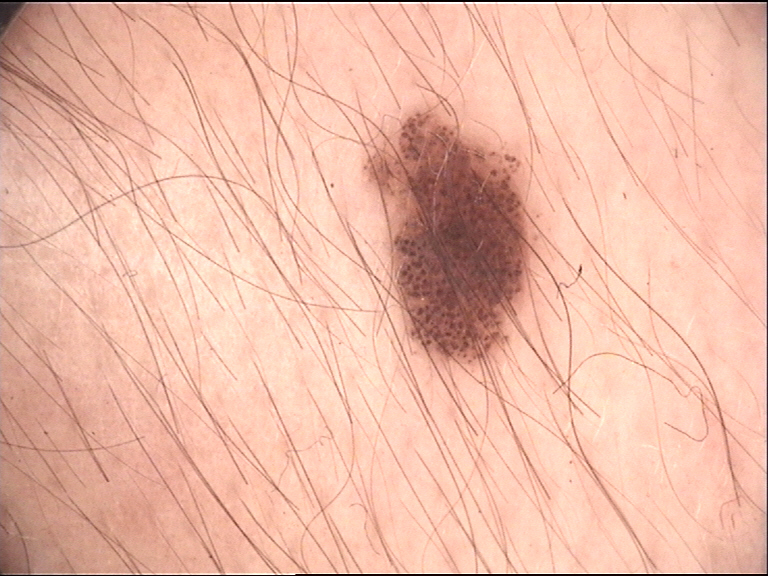The diagnosis was a dysplastic junctional nevus.